A female patient 73 years of age. A clinical photo of a skin lesion taken with a smartphone — 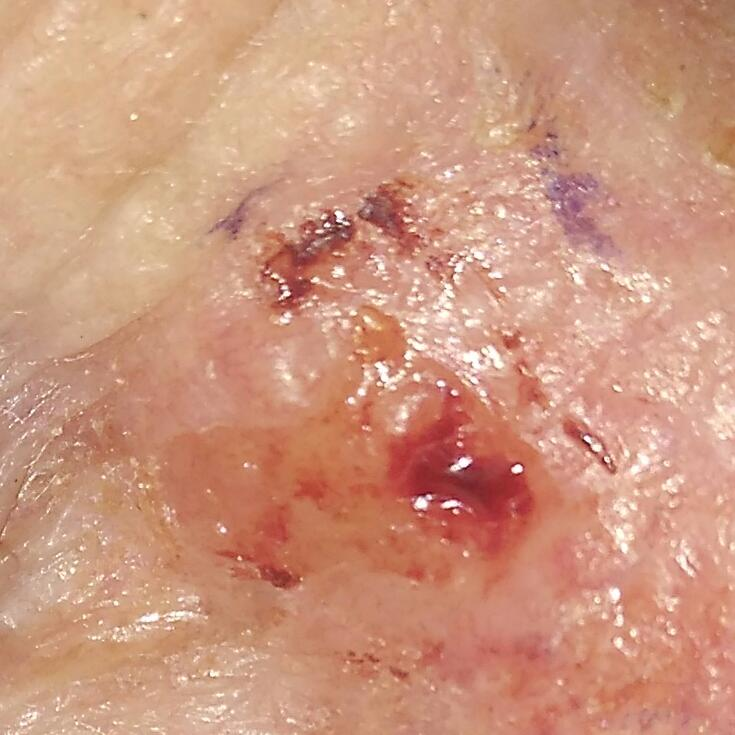  lesion_location: the nose
  symptoms:
    present:
      - bleeding
      - growth
      - pain
      - elevation
      - itching
  diagnosis:
    name: basal cell carcinoma
    code: BCC
    malignancy: malignant
    confirmation: histopathology